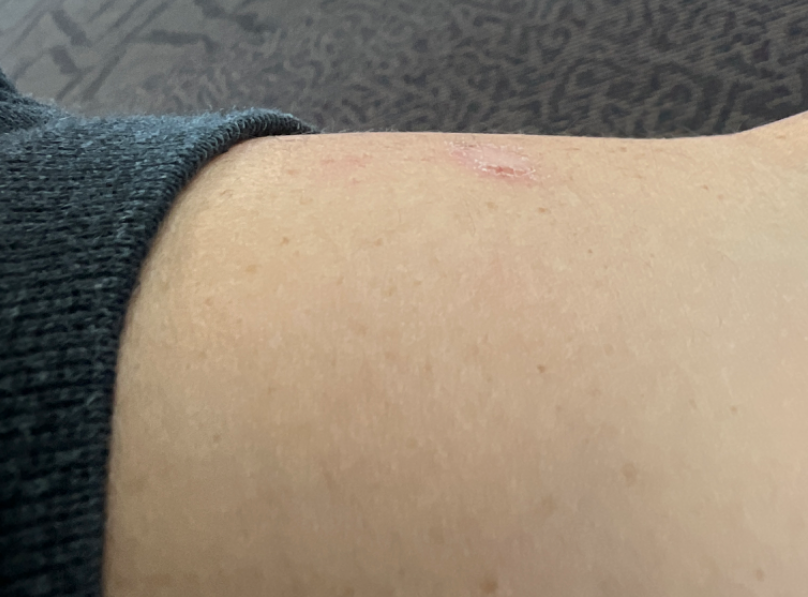Case summary:
- assessment — ungradable on photographic review
- affected area — arm
- subject — female
- described texture — rough or flaky
- other reported symptoms — none reported
- framing — at an angle
- patient describes the issue as — a rash
- symptoms — bothersome appearance and enlargement
- onset — one to four weeks